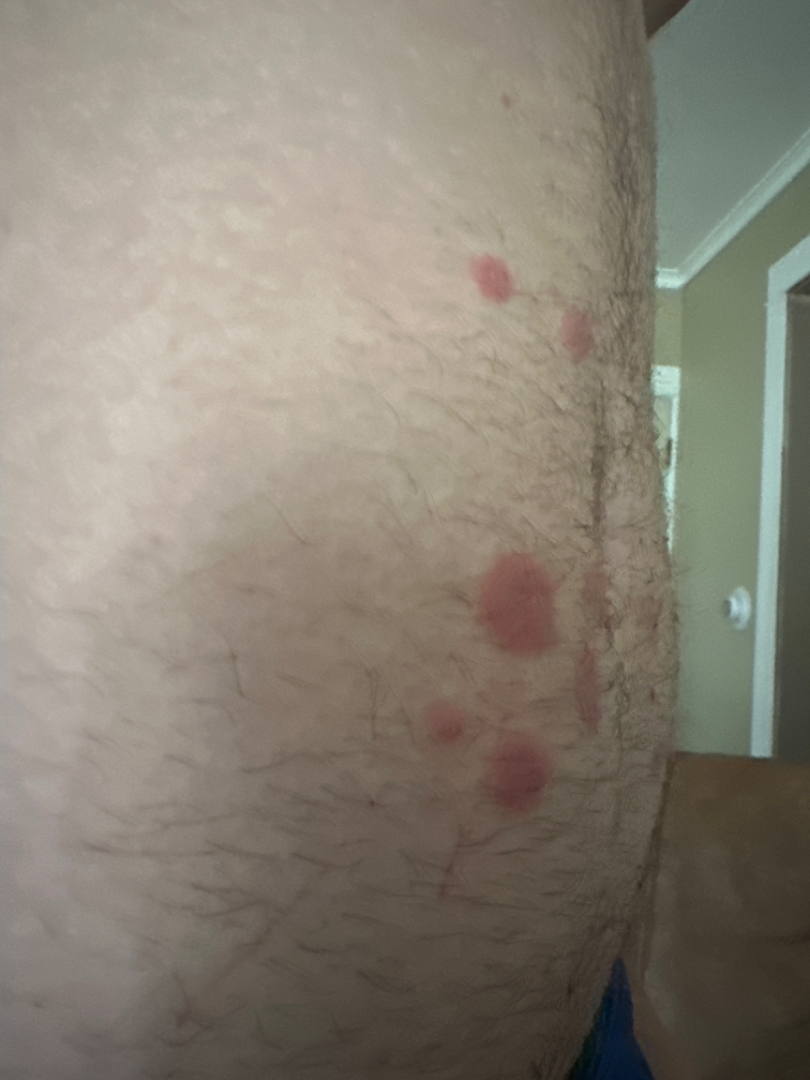| field | value |
|---|---|
| anatomic site | front of the torso |
| framing | at an angle |
| skin tone | FST II |
| described texture | raised or bumpy |
| diagnostic considerations | favoring Insect Bite; an alternative is Sweet syndrome |